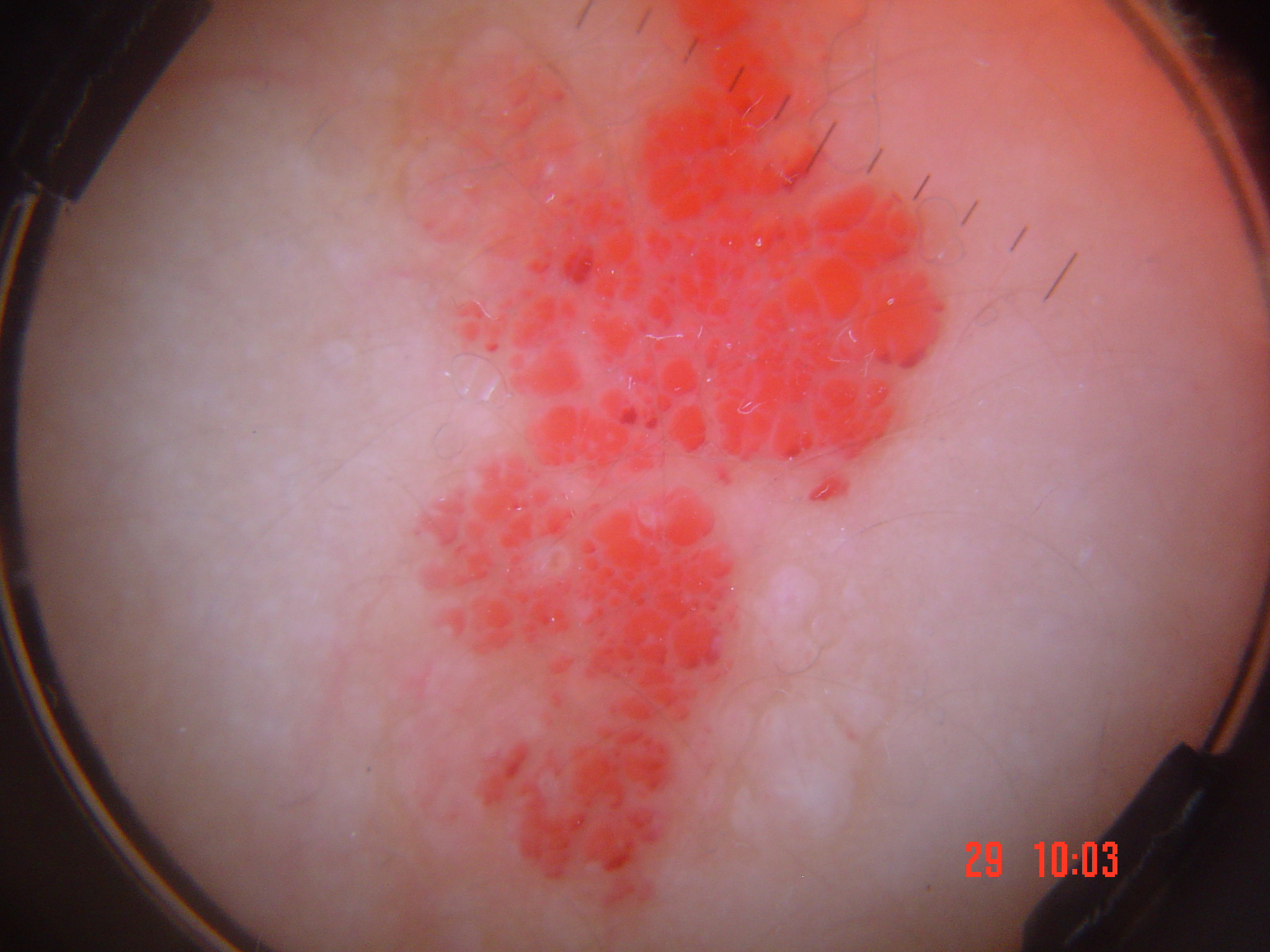Q: What is the imaging modality?
A: dermoscopy
Q: What is the lesion category?
A: vascular
Q: What is this lesion?
A: lymphangioma (expert consensus)